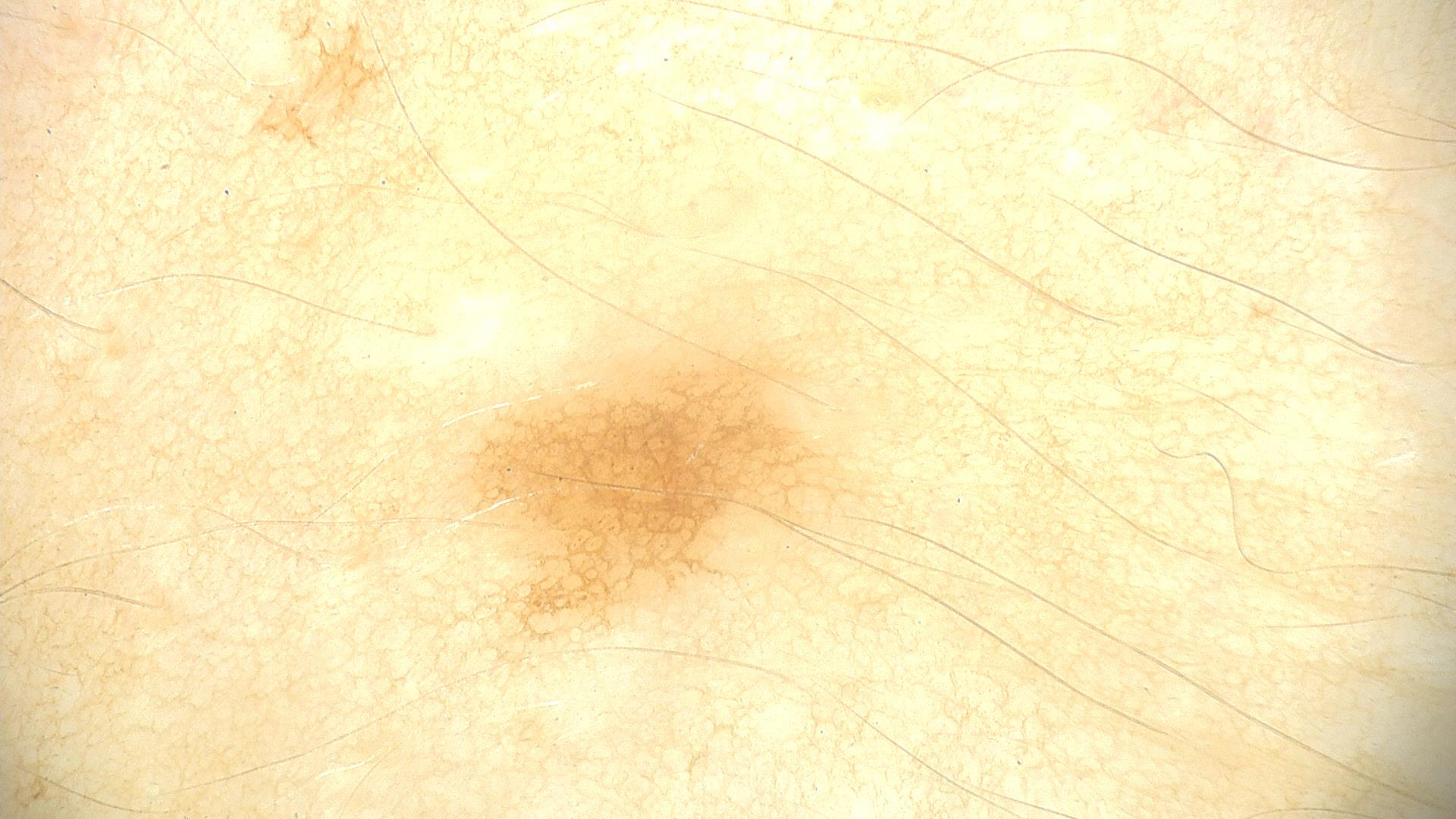Labeled as a dysplastic junctional nevus.